The lesion is associated with itching · texture is reported as raised or bumpy · the patient is female · the arm is involved · this image was taken at an angle: 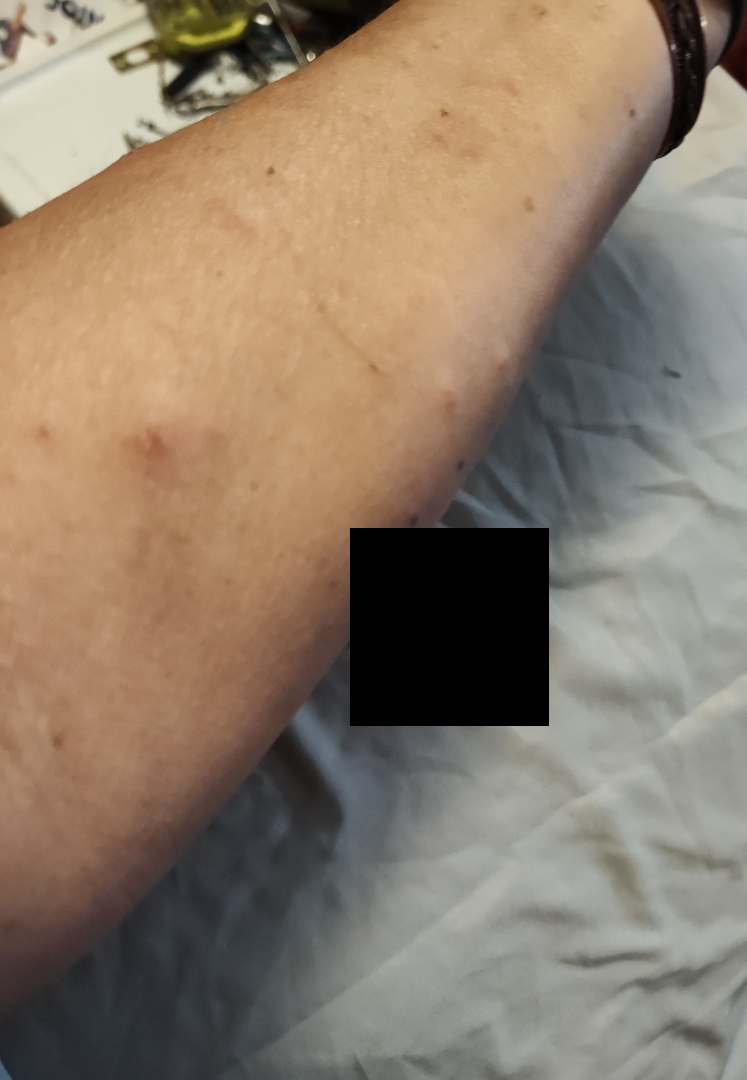{"differential": {"tied_lead": ["Granuloma annulare", "Skin and soft tissue atypical mycobacterial infection", "Eczema", "Allergic Contact Dermatitis"]}}